A dermoscopy image of a single skin lesion: 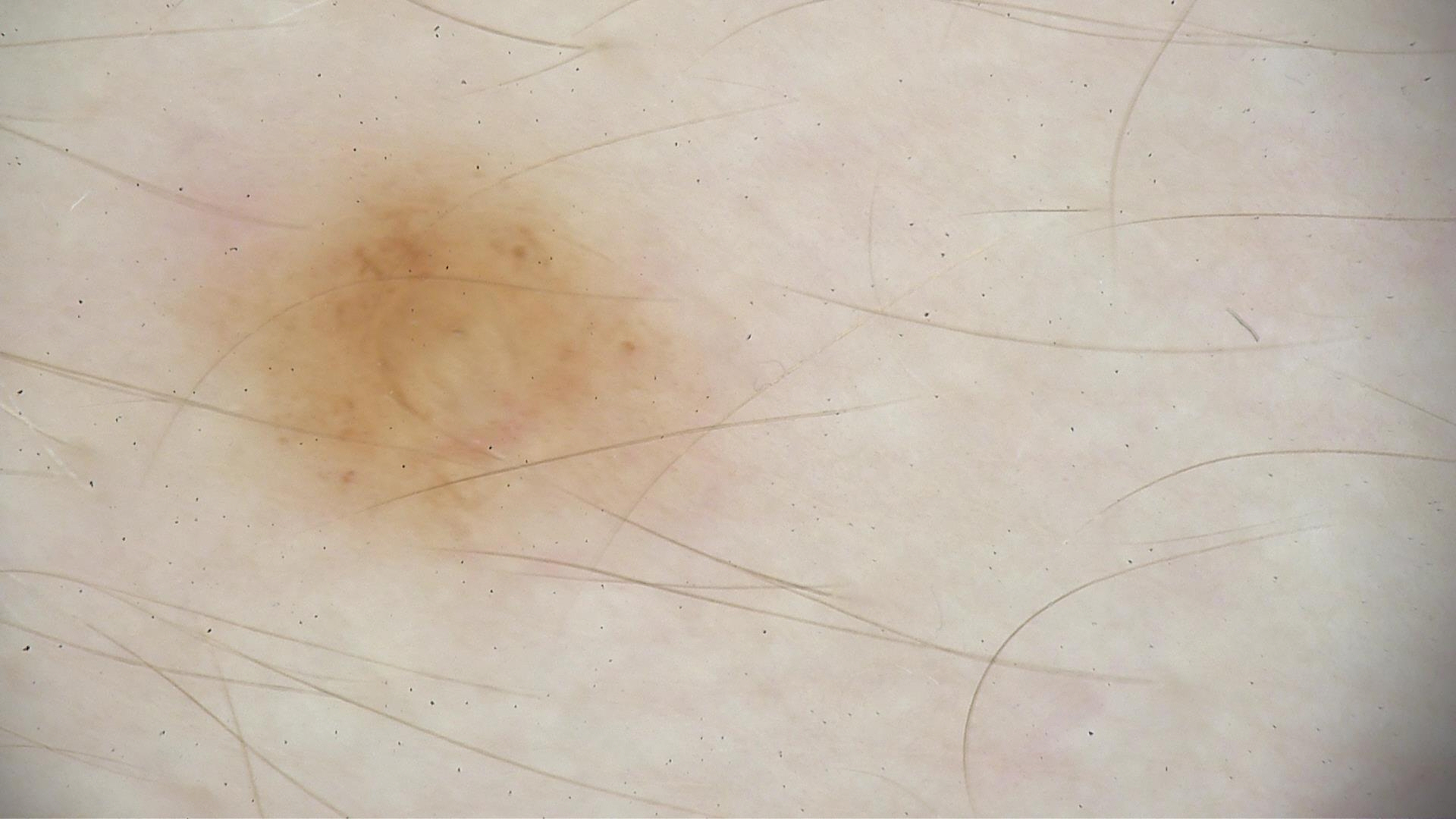Q: What is this lesion?
A: dysplastic junctional nevus (expert consensus)